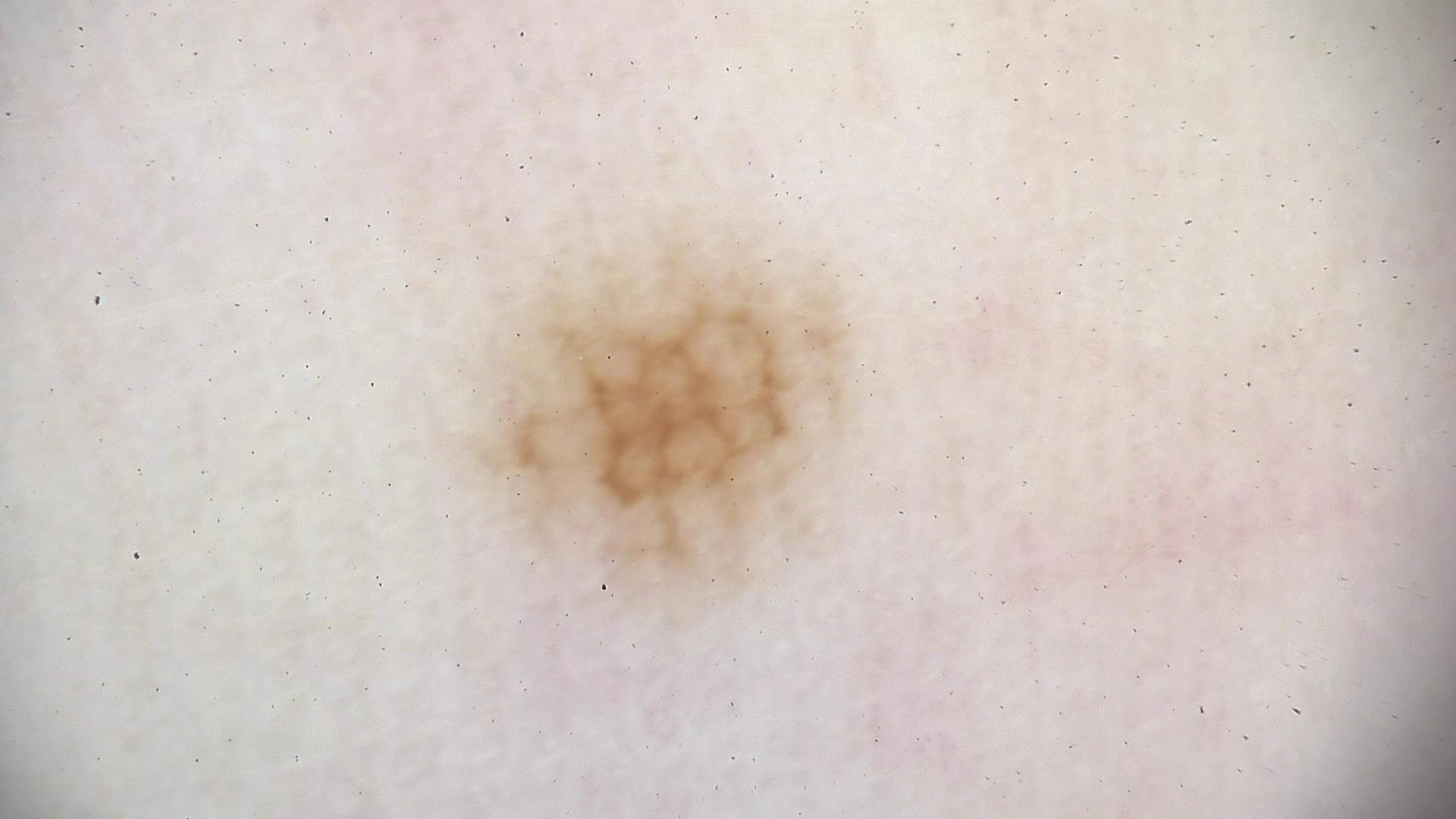image: dermoscopy
label: acral dysplastic junctional nevus (expert consensus)